A dermoscopic photograph of a skin lesion.
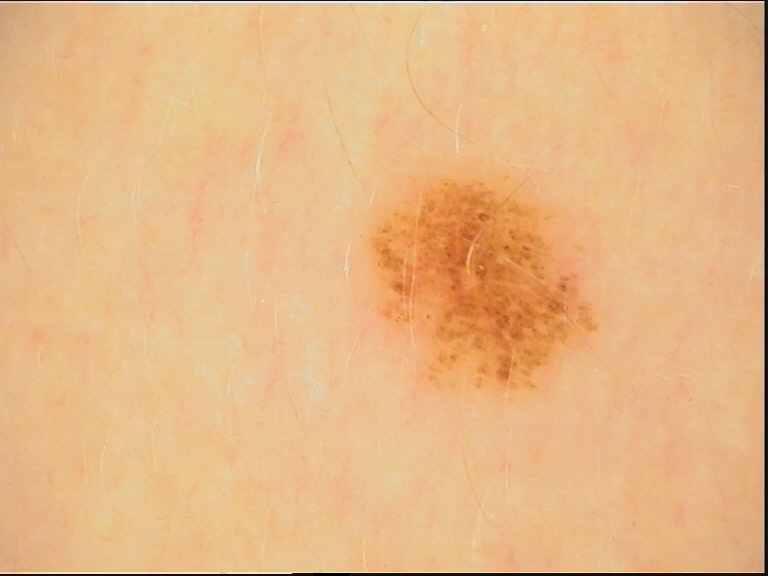Diagnosed as a dysplastic junctional nevus.